The patient is a female approximately 50 years of age; a dermoscopic view of a skin lesion.
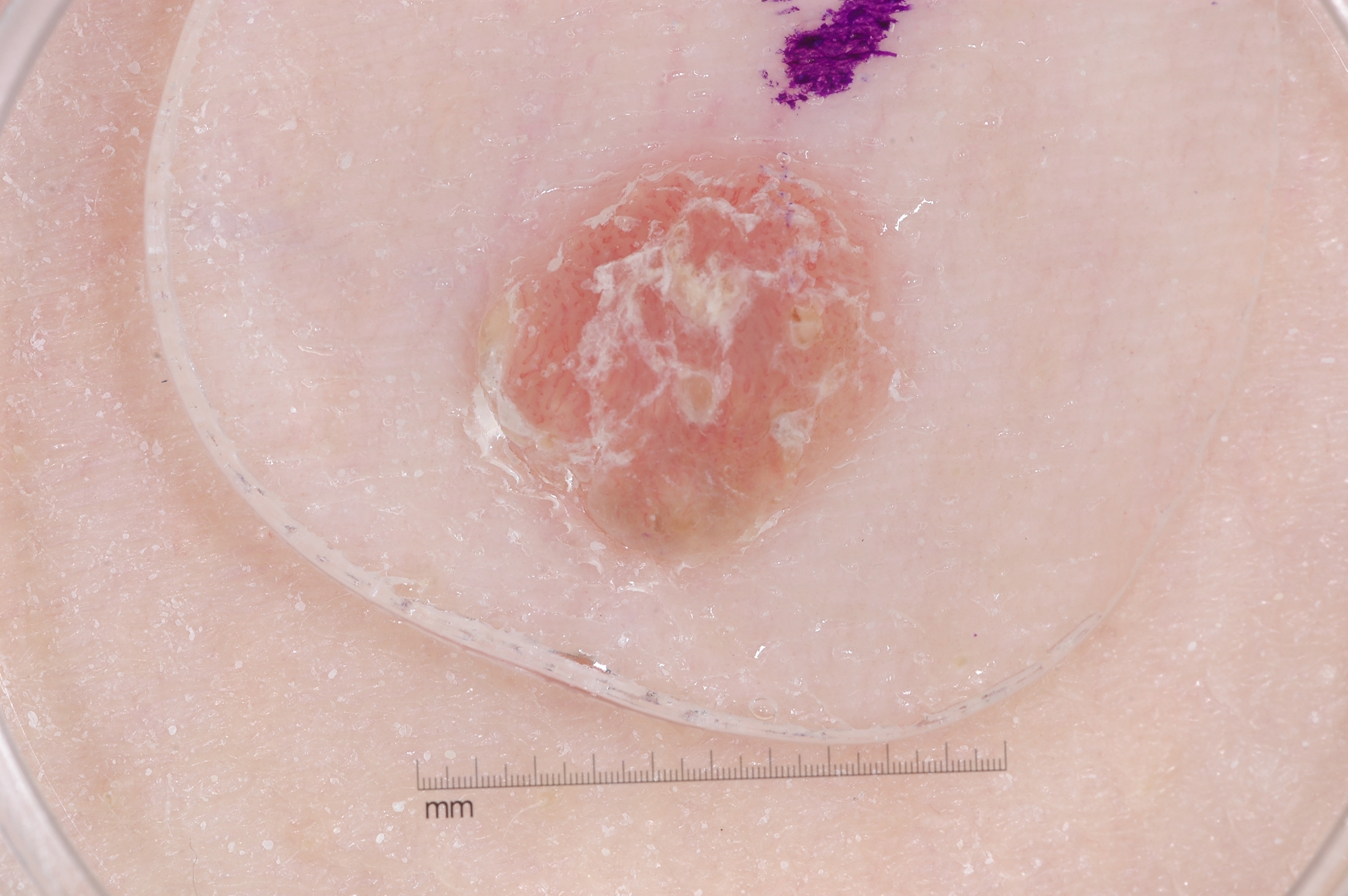Image and clinical context:
In (x1, y1, x2, y2) order, the lesion is bounded by 474, 140, 906, 567. Dermoscopic review identifies milia-like cysts. The lesion takes up a moderate portion of the field.
Impression:
The lesion was assessed as a seborrheic keratosis, a benign lesion.